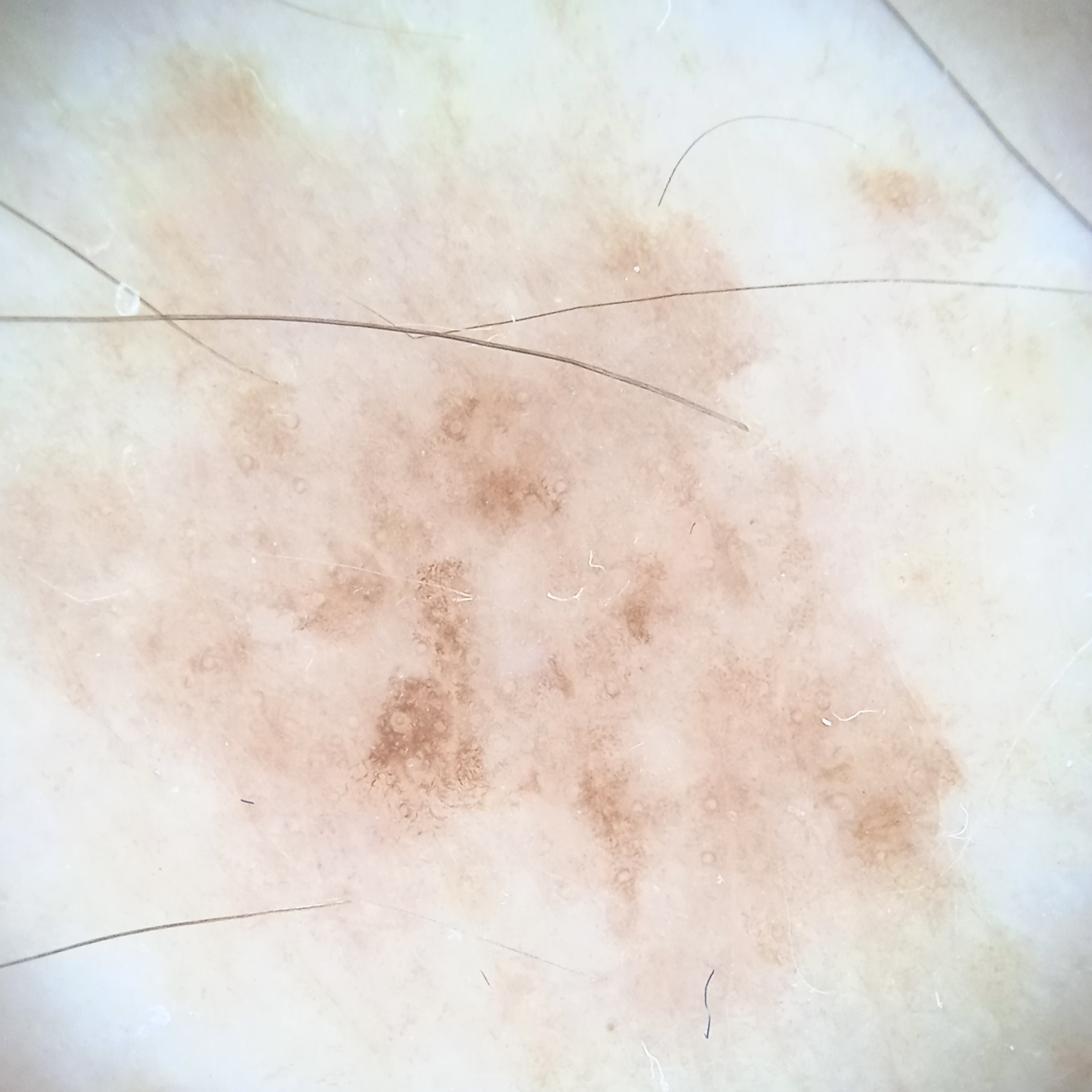{"diagnosis": {"name": "melanoma", "malignancy": "malignant"}}